A dermoscopic image of a skin lesion.
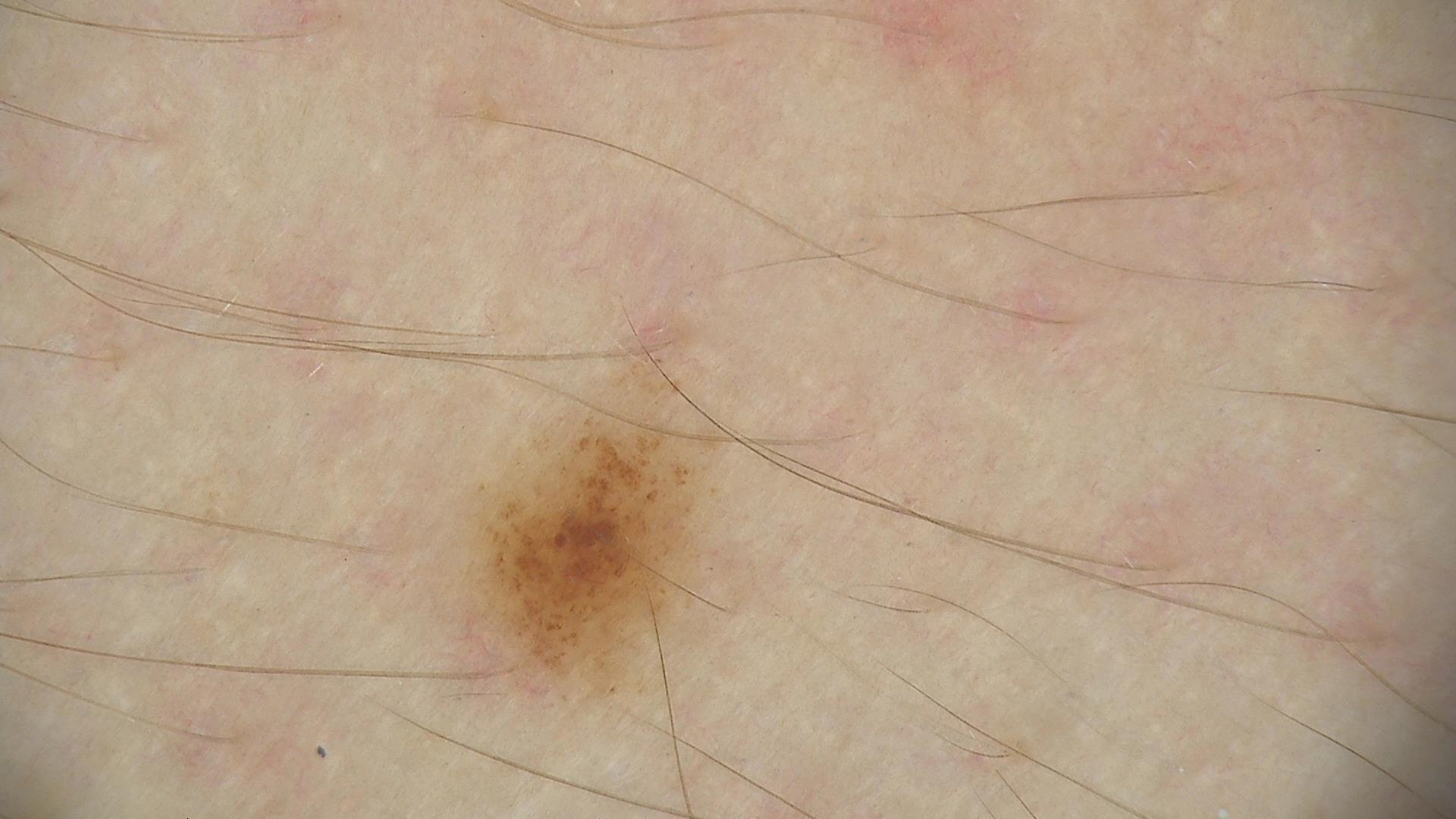The diagnosis was a benign lesion — a dysplastic junctional nevus.